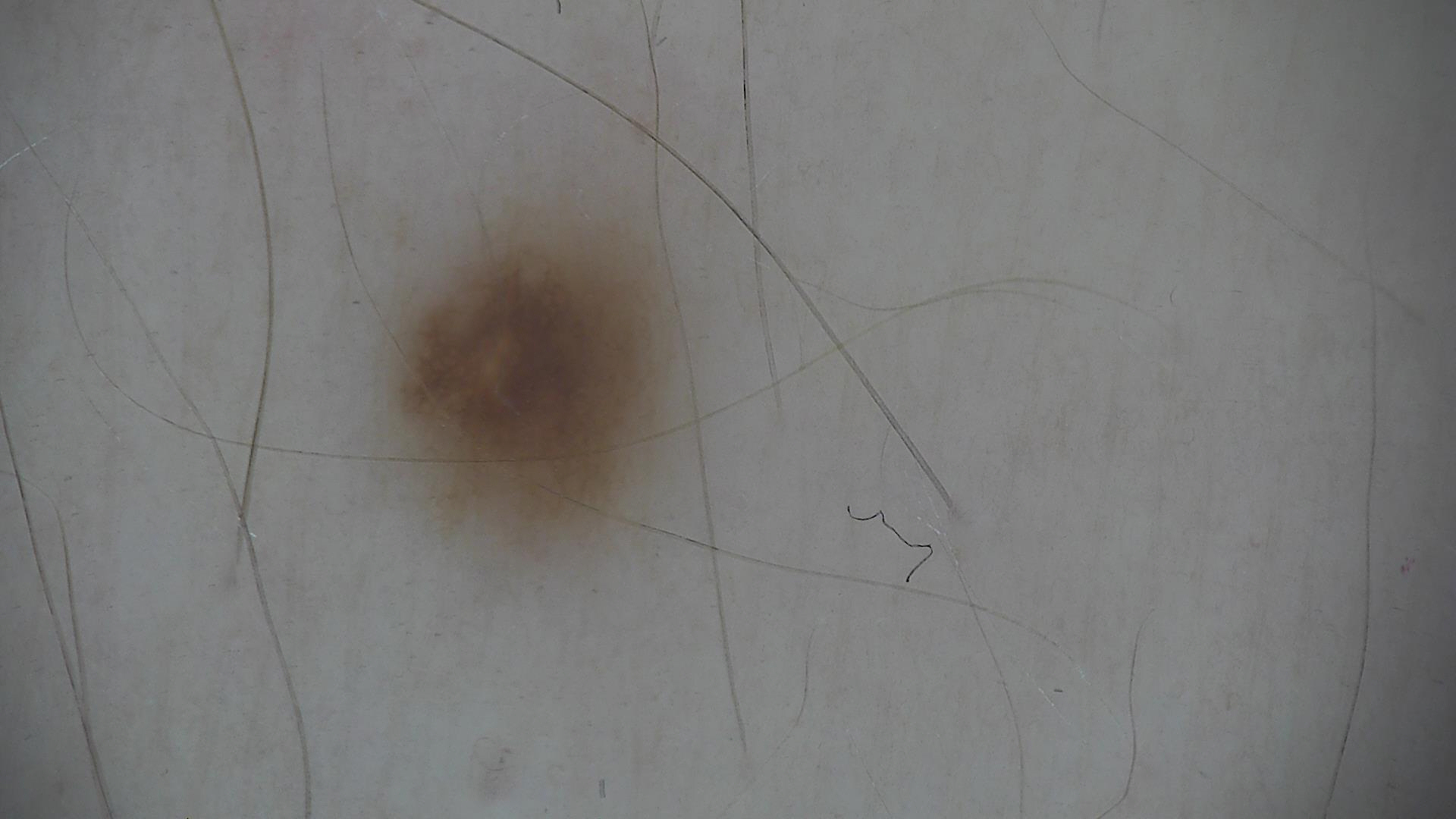A dermatoscopic image of a skin lesion.
Classified as a benign lesion — a dysplastic junctional nevus.